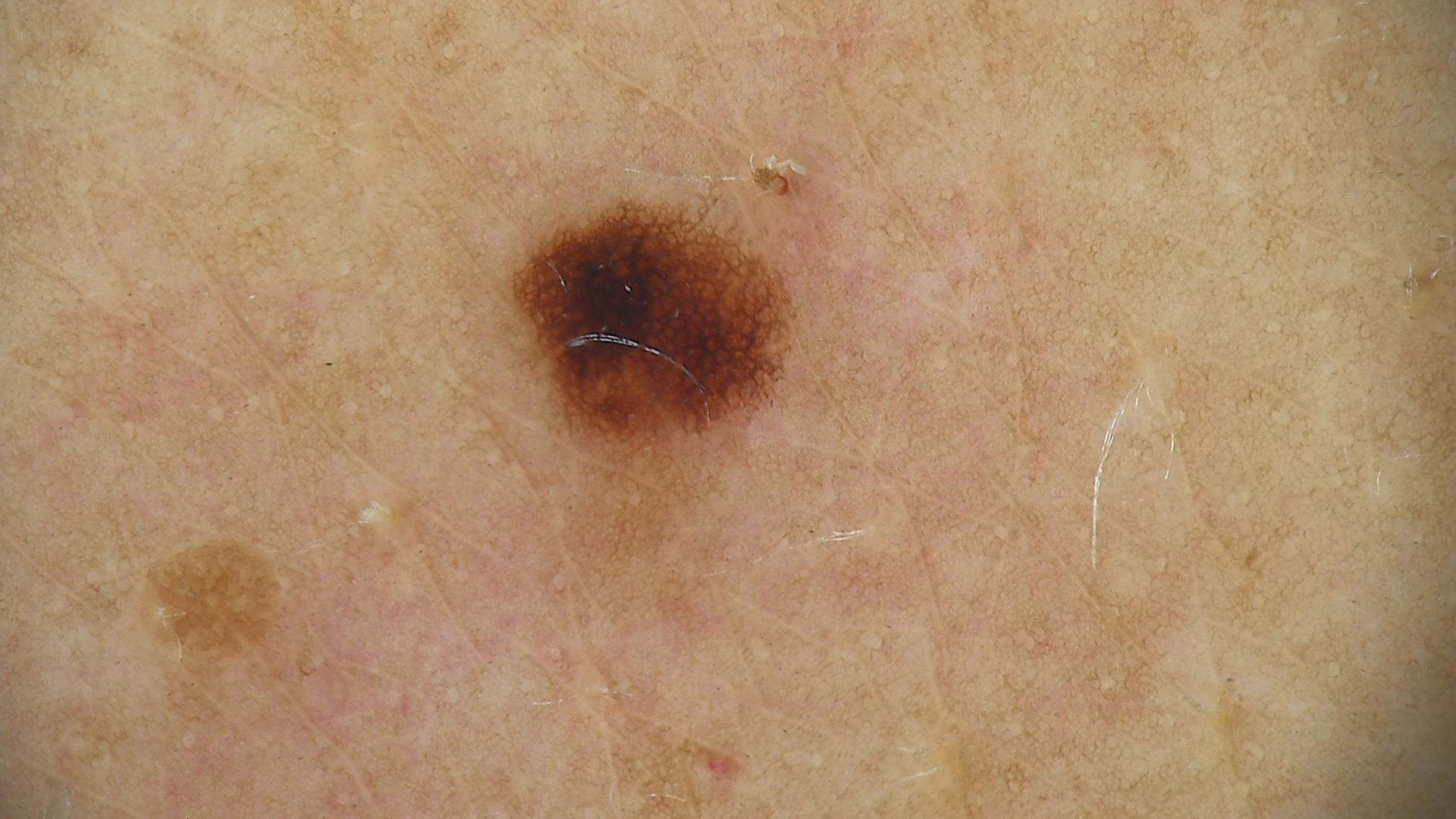Dermoscopy of a skin lesion. Diagnosed as a dysplastic junctional nevus.